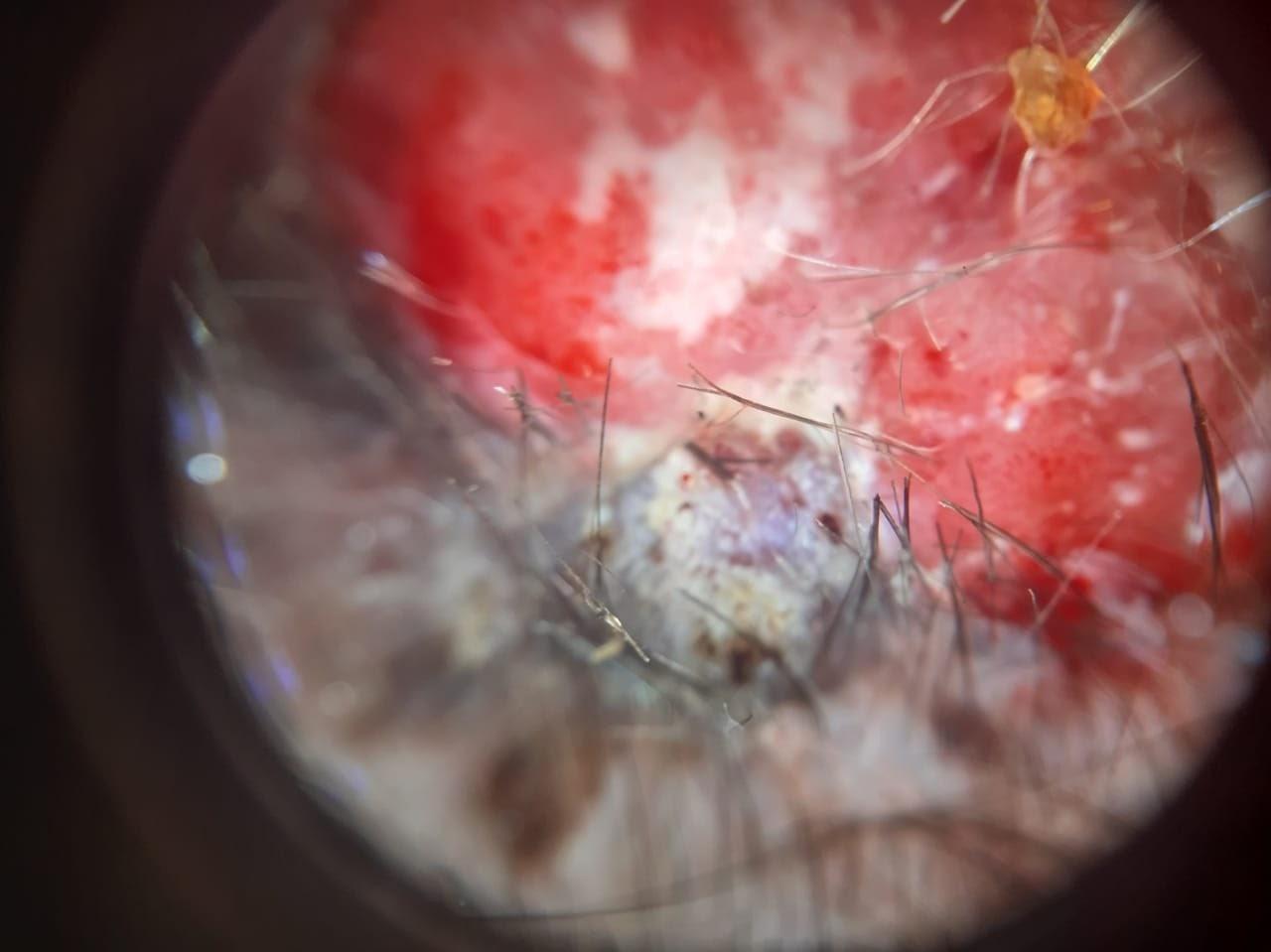diagnosis — Melanoma (biopsy-proven).